A female patient age 81; the chart notes prior skin cancer (patient or family); the patient is Fitzpatrick skin type II: 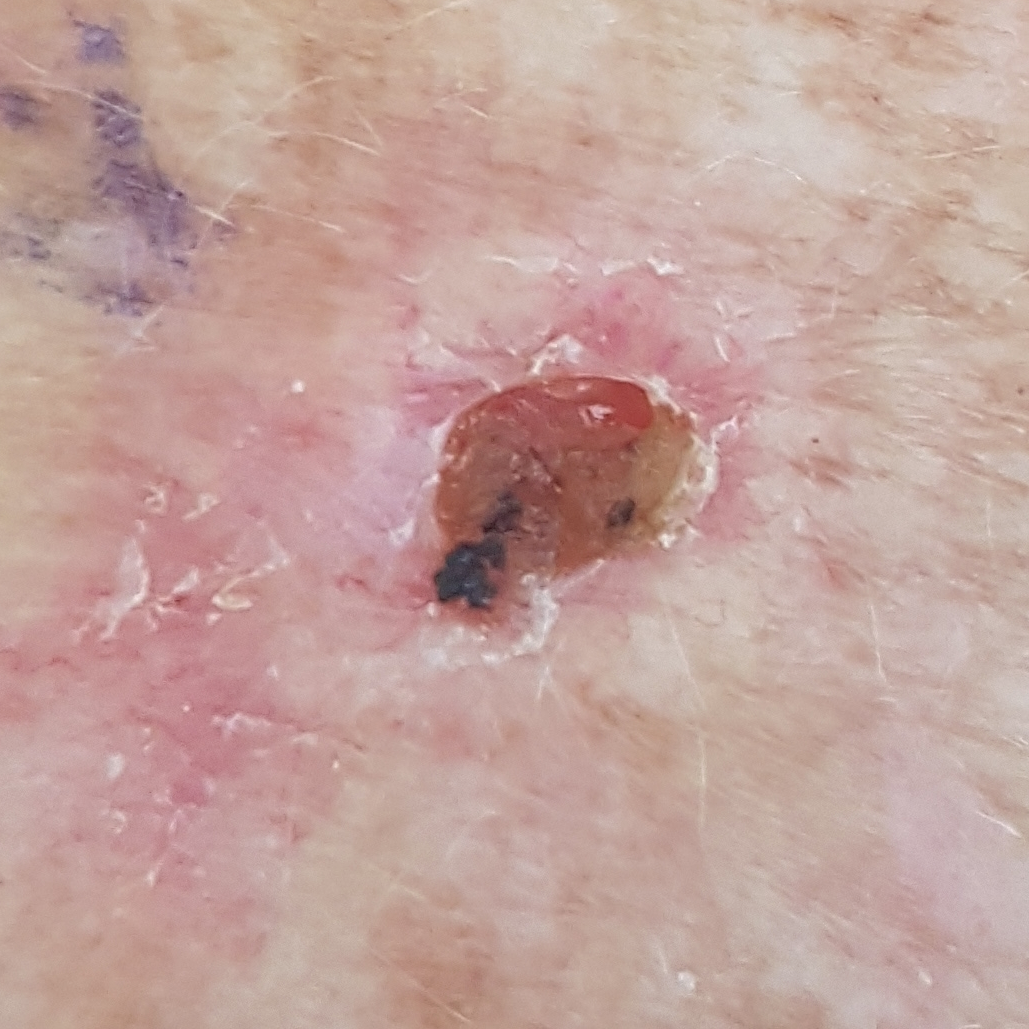{
  "lesion_size": {
    "diameter_1_mm": 7.0,
    "diameter_2_mm": 18.0
  },
  "symptoms": {
    "present": [
      "growth",
      "bleeding",
      "itching",
      "elevation"
    ],
    "absent": [
      "change in appearance"
    ]
  },
  "diagnosis": {
    "name": "basal cell carcinoma",
    "code": "BCC",
    "malignancy": "malignant",
    "confirmation": "histopathology"
  }
}